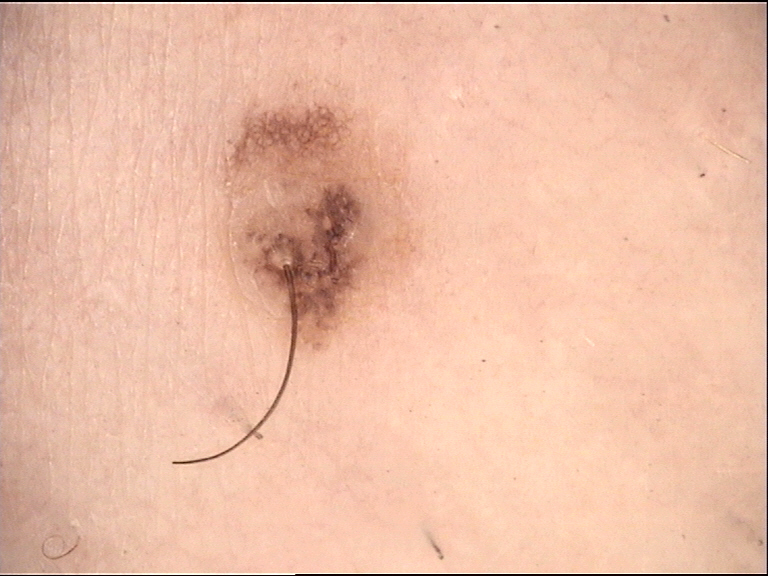Q: What is the diagnosis?
A: congenital compound nevus (expert consensus)